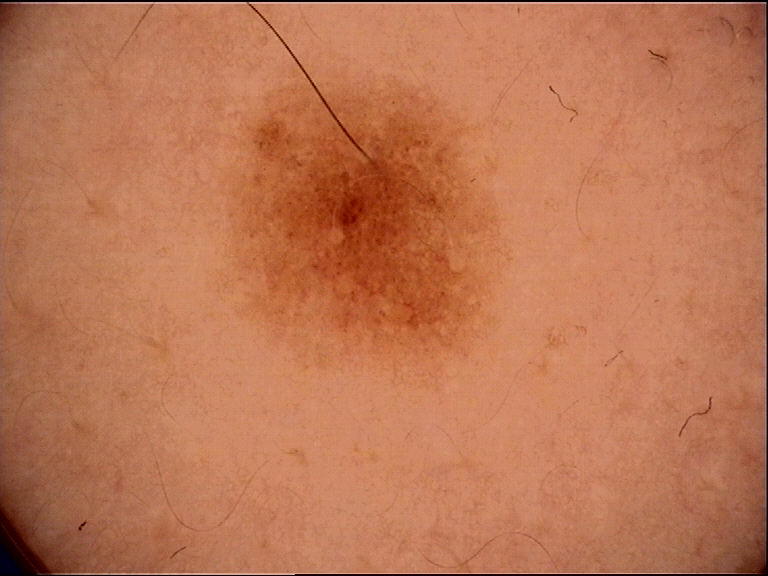A dermoscopy image of a single skin lesion. The diagnostic label was a dysplastic junctional nevus.